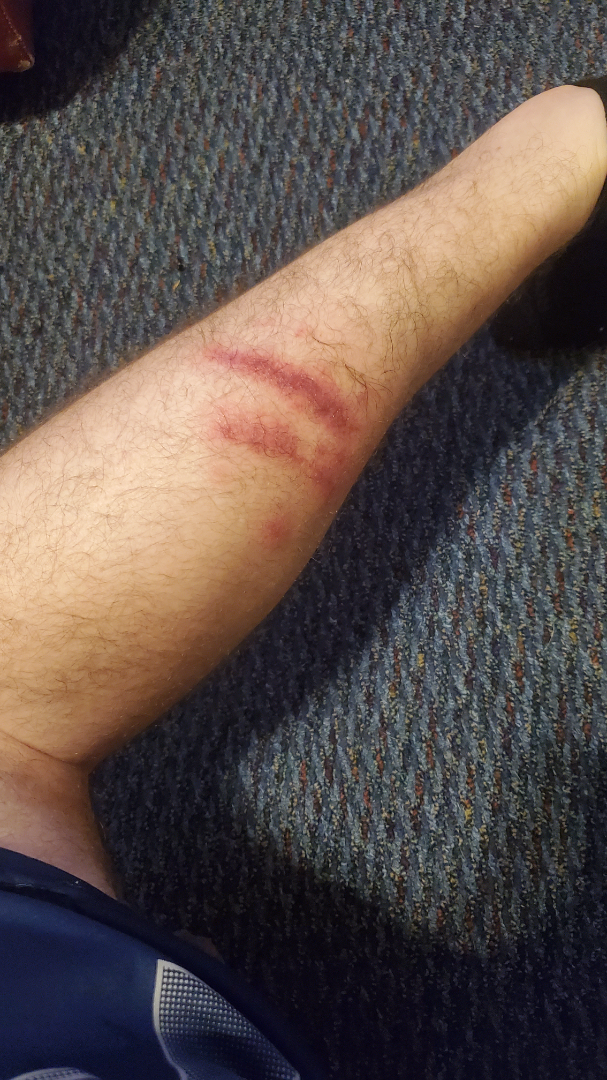{
  "differential": {
    "tied_lead": [
      "Abrasion, scrape, or scab",
      "Flagellate erythema"
    ],
    "unlikely": [
      "Allergic Contact Dermatitis",
      "Skin infection",
      "Dermatomyositis",
      "Animal bite - wound"
    ]
  }
}